A dermatoscopic image of a skin lesion.
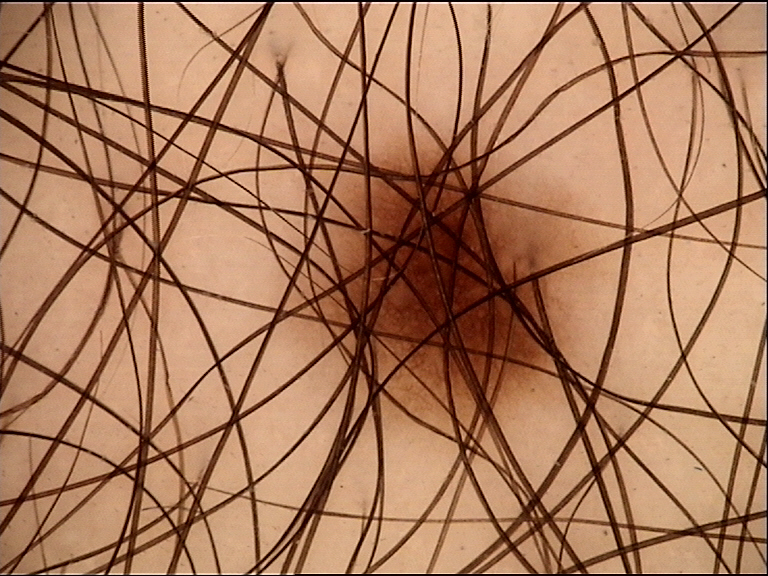Q: What is the diagnosis?
A: junctional nevus (expert consensus)